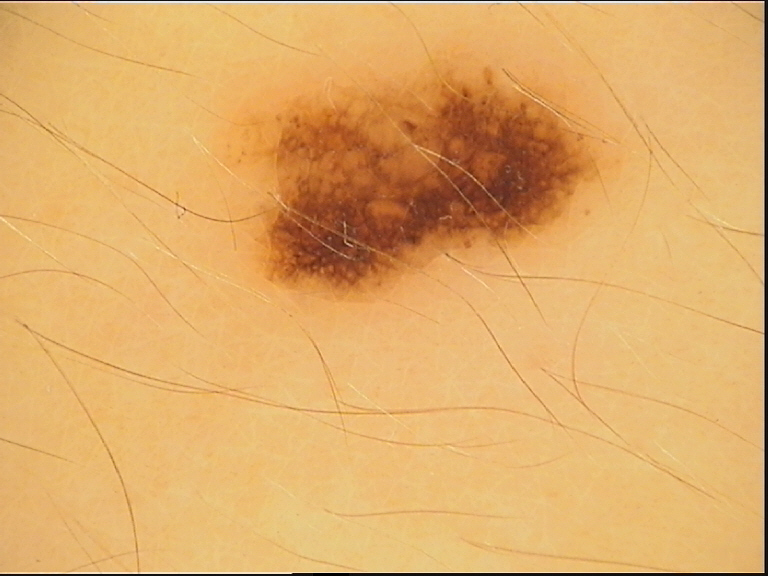A dermoscopic image of a skin lesion. Labeled as a dysplastic junctional nevus.